A female subject aged around 60:
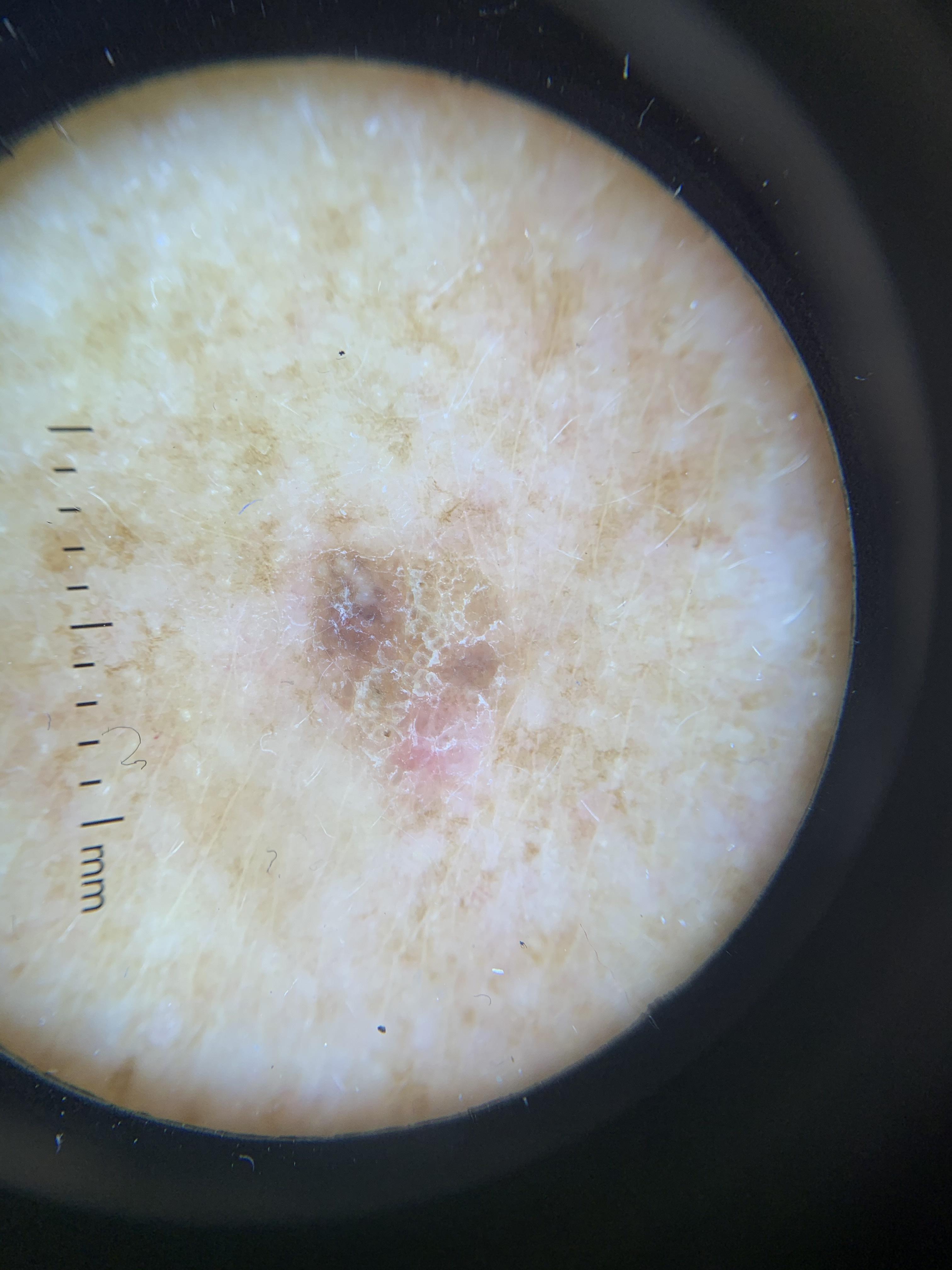Image and clinical context:
The lesion is on the trunk, specifically the posterior trunk.
Conclusion:
On biopsy, the diagnosis was a seborrheic keratosis.